Close-up view: 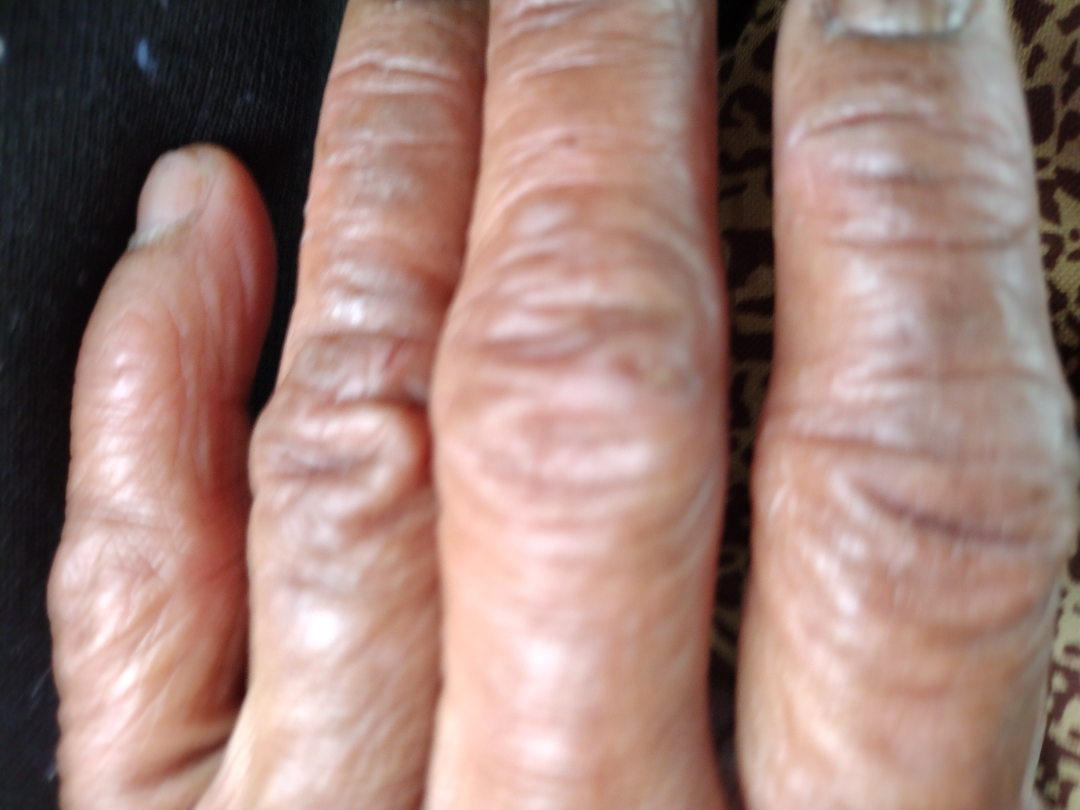The reviewer was unable to grade this case for skin condition.